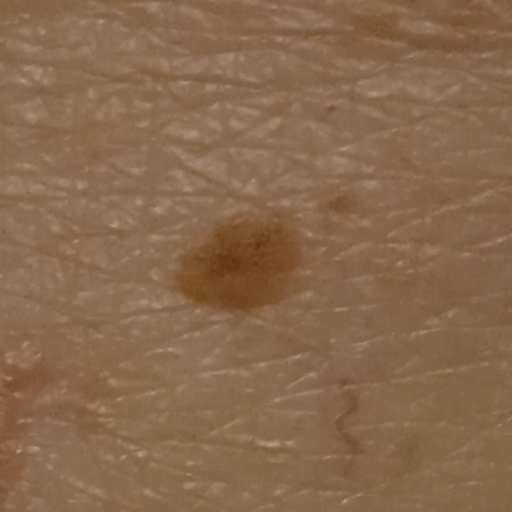A clinical photograph showing a skin lesion. A female subject aged 84. The patient says their skin tans without first burning. Measuring roughly 5.9 mm. The diagnostic impression was a seborrheic keratosis.